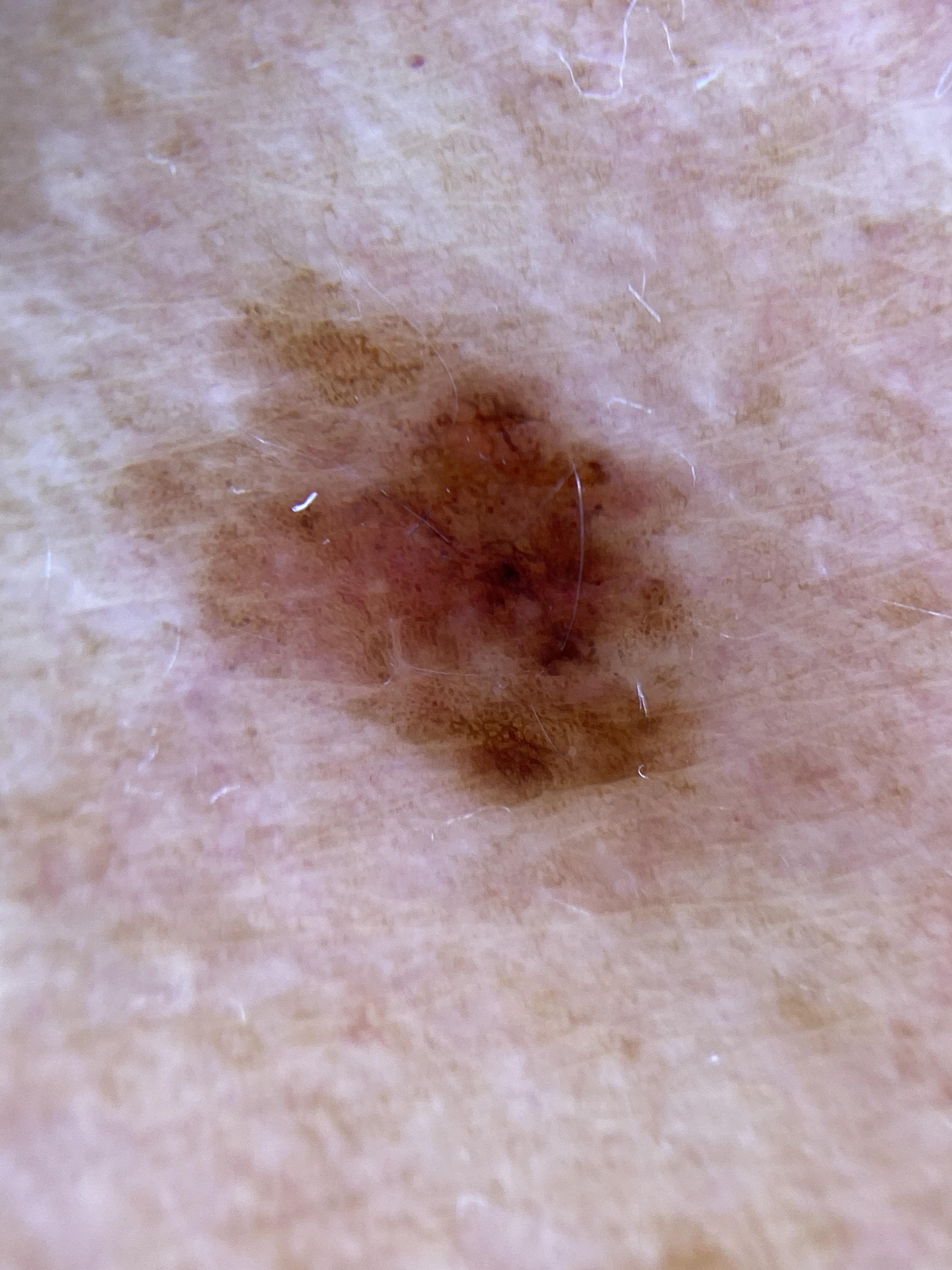A male subject roughly 70 years of age. Confirmed on histopathology as a benign lesion — a nevus.